A dermoscopic close-up of a skin lesion · a male patient roughly 40 years of age: 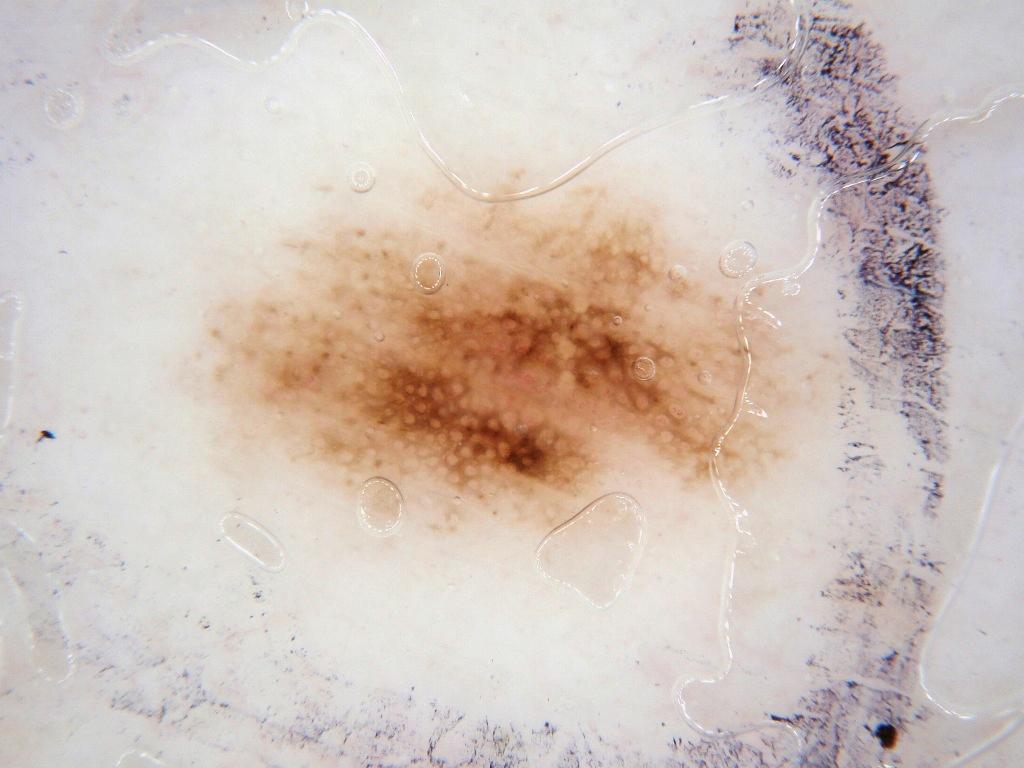The lesion takes up a moderate portion of the field. Dermoscopy demonstrates globules and pigment network. As (left, top, right, bottom), the lesion occupies the region <bbox>207, 184, 800, 532</bbox>. Consistent with a melanocytic nevus.